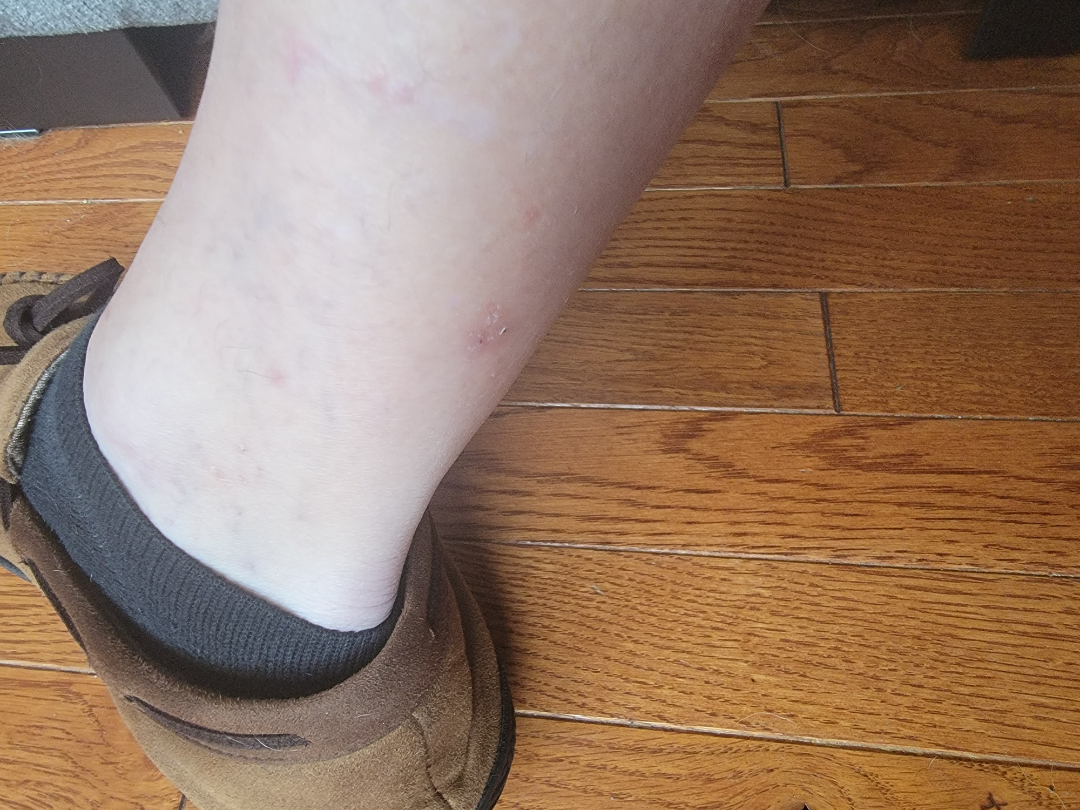The photo was captured at a distance.
Skin tone: Fitzpatrick phototype I; lay reviewers estimated Monk skin tone scale 1 or 2 (two reviewer pools).
Located on the leg.
The patient considered this a rash.
Reported duration is one to four weeks.
On photographic review, Acute and chronic dermatitis (possible); Irritant Contact Dermatitis (possible).